The patient reported no systemic symptoms; the contributor is 18–29, female; the patient described the issue as a rash; the patient notes the lesion is raised or bumpy and fluid-filled; close-up view; the affected area is the arm; present for one to four weeks:
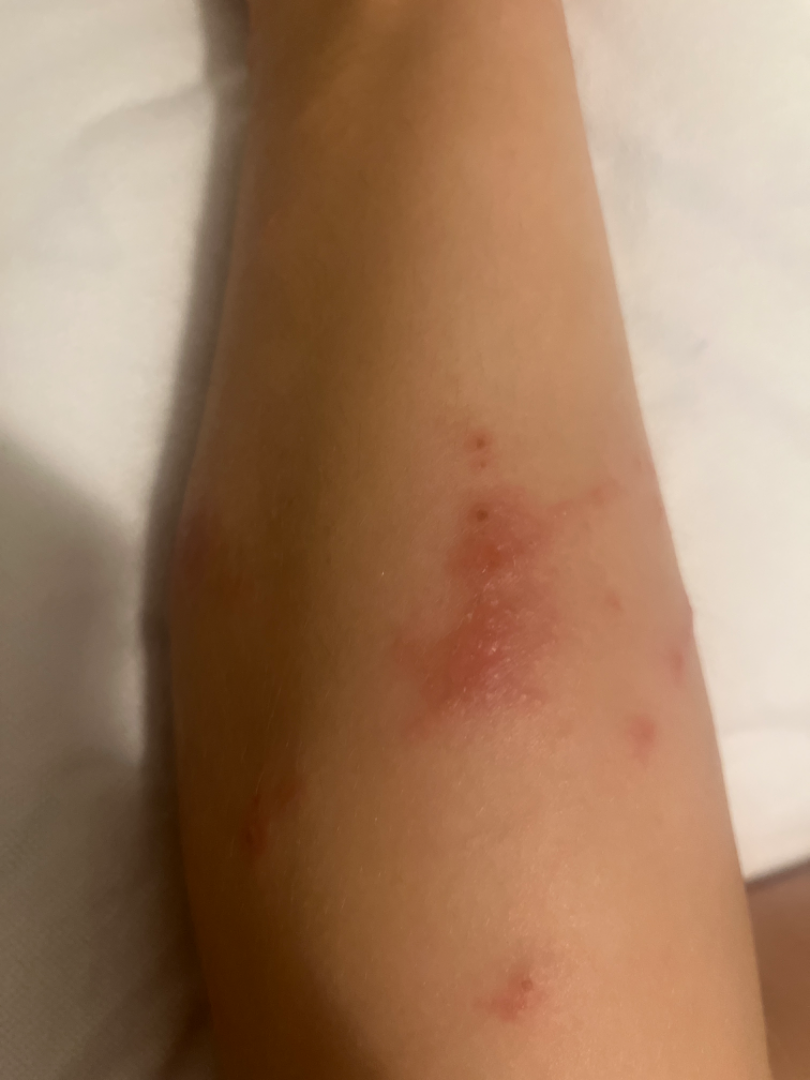The case was indeterminate on photographic review.